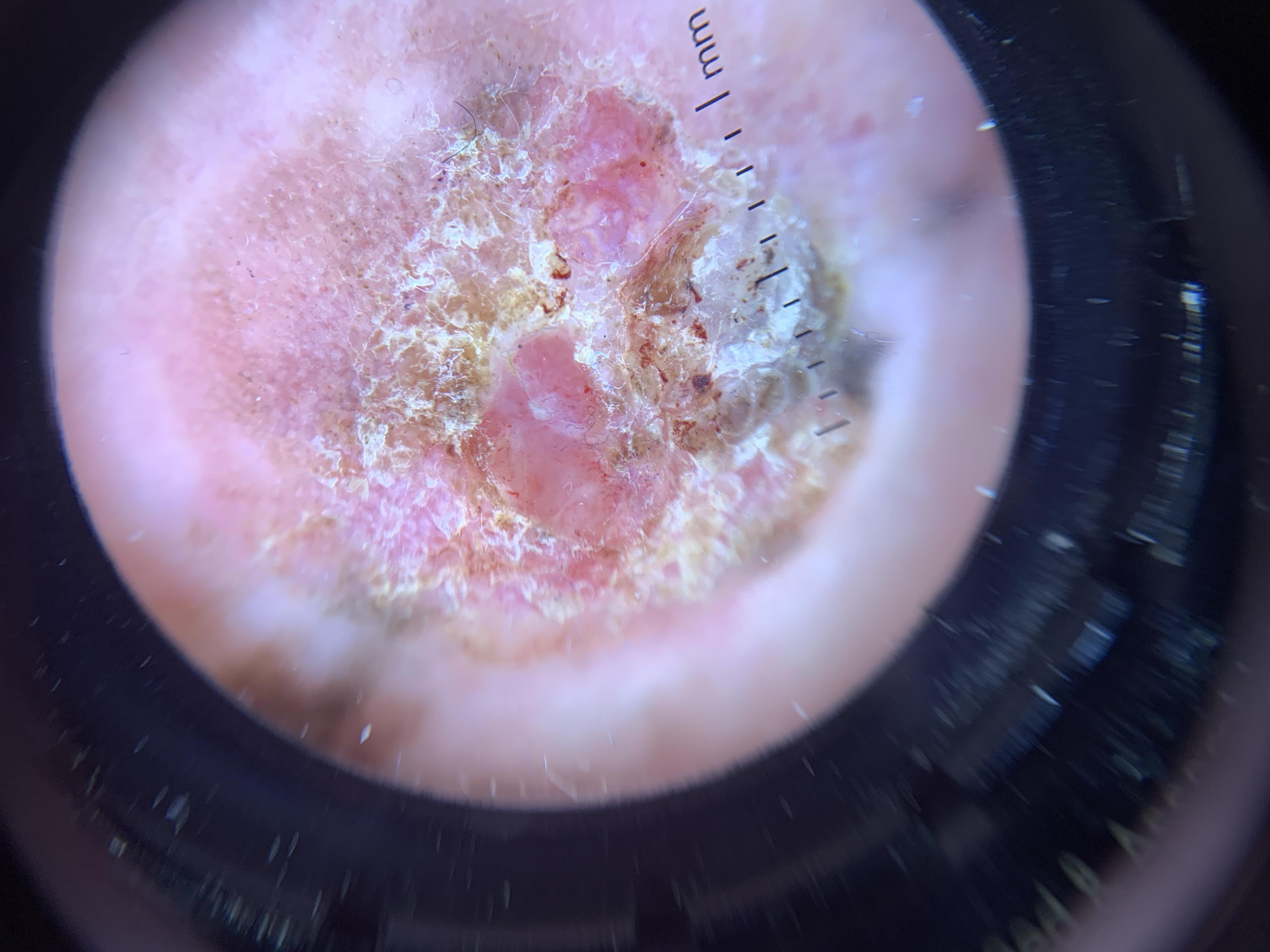<case>
<image>dermoscopic image</image>
<skin_type>II</skin_type>
<patient>
<age_approx>80</age_approx>
<sex>female</sex>
</patient>
<diagnosis>
<name>Melanoma</name>
<malignancy>malignant</malignancy>
<confirmation>histopathology</confirmation>
</diagnosis>
</case>